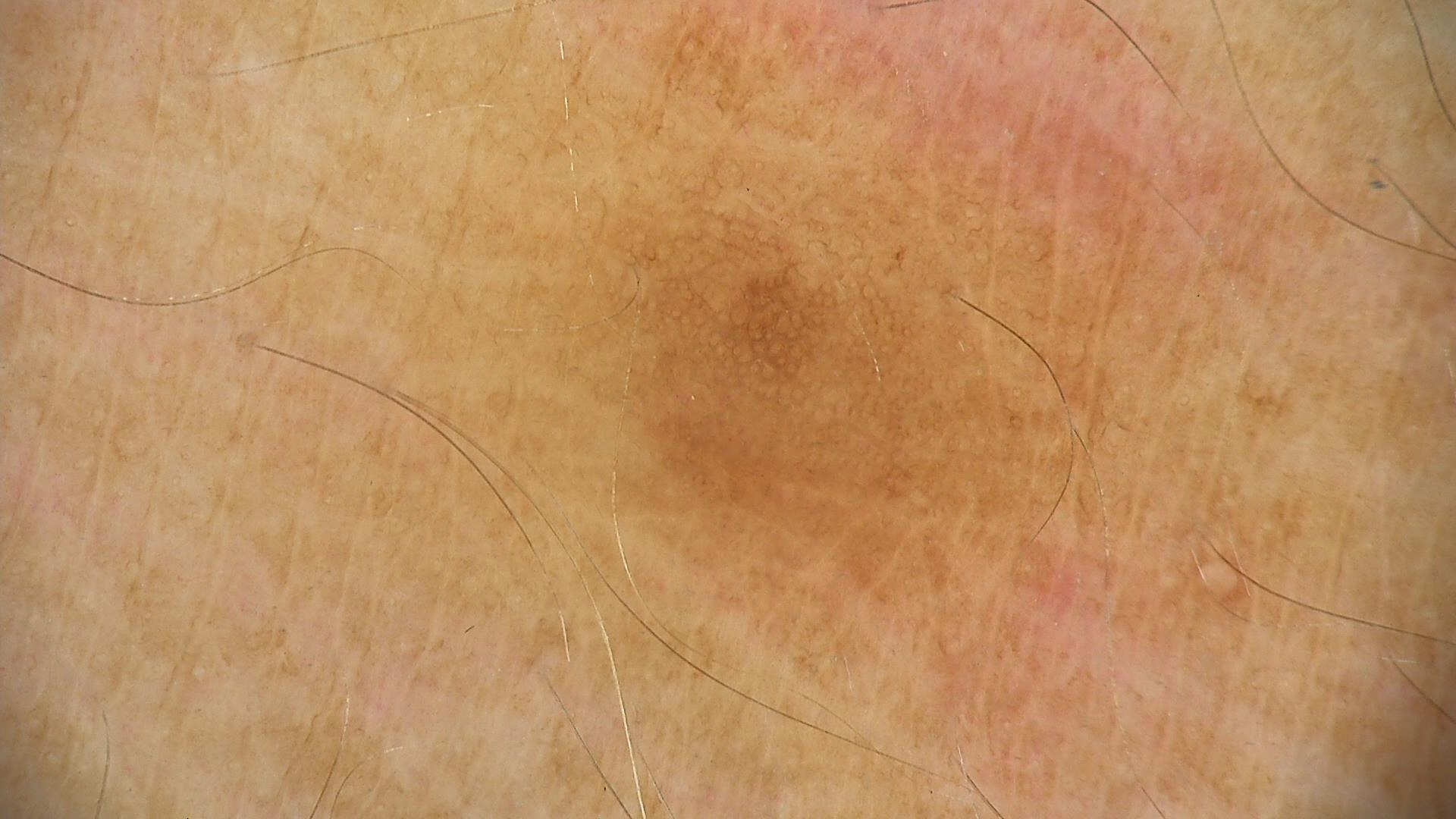A skin lesion imaged with a dermatoscope. Diagnosed as a solar lentigo.